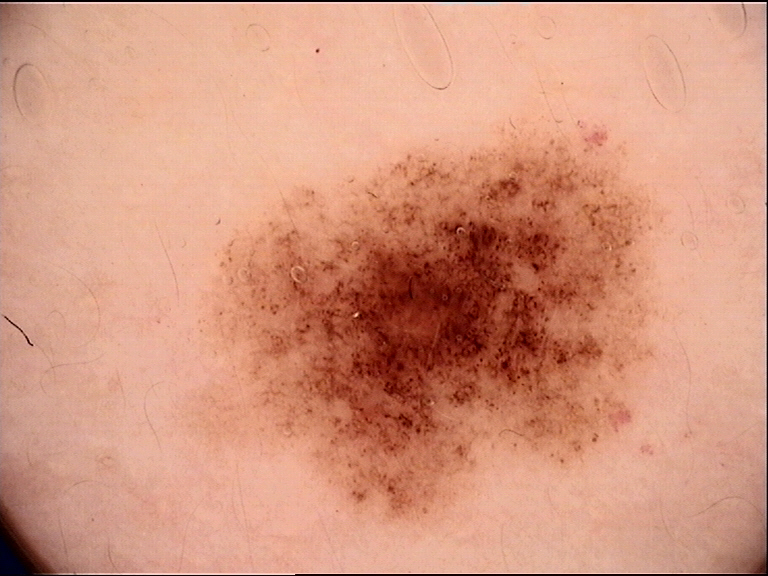The diagnosis was a dysplastic junctional nevus.